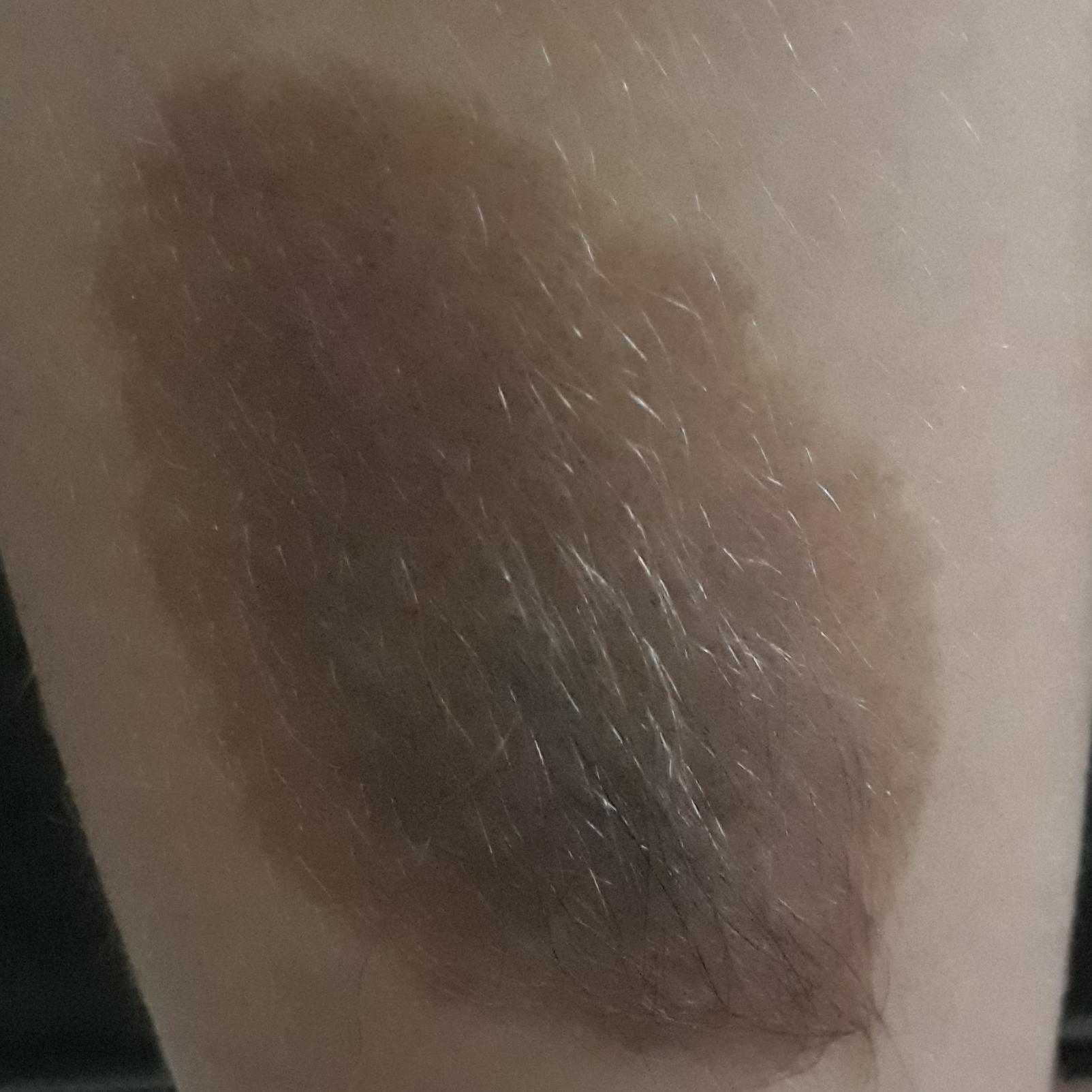Located on a thigh.
The diagnostic impression was a nevus.